A skin lesion imaged with a dermatoscope · by self-report, a personal history of skin cancer and a personal history of cancer · a moderate number of moles by the patient's own estimate · the patient says their skin reddens with sun exposure · imaged for a research study, with no referral diagnosis recorded · a male subject 77 years of age — 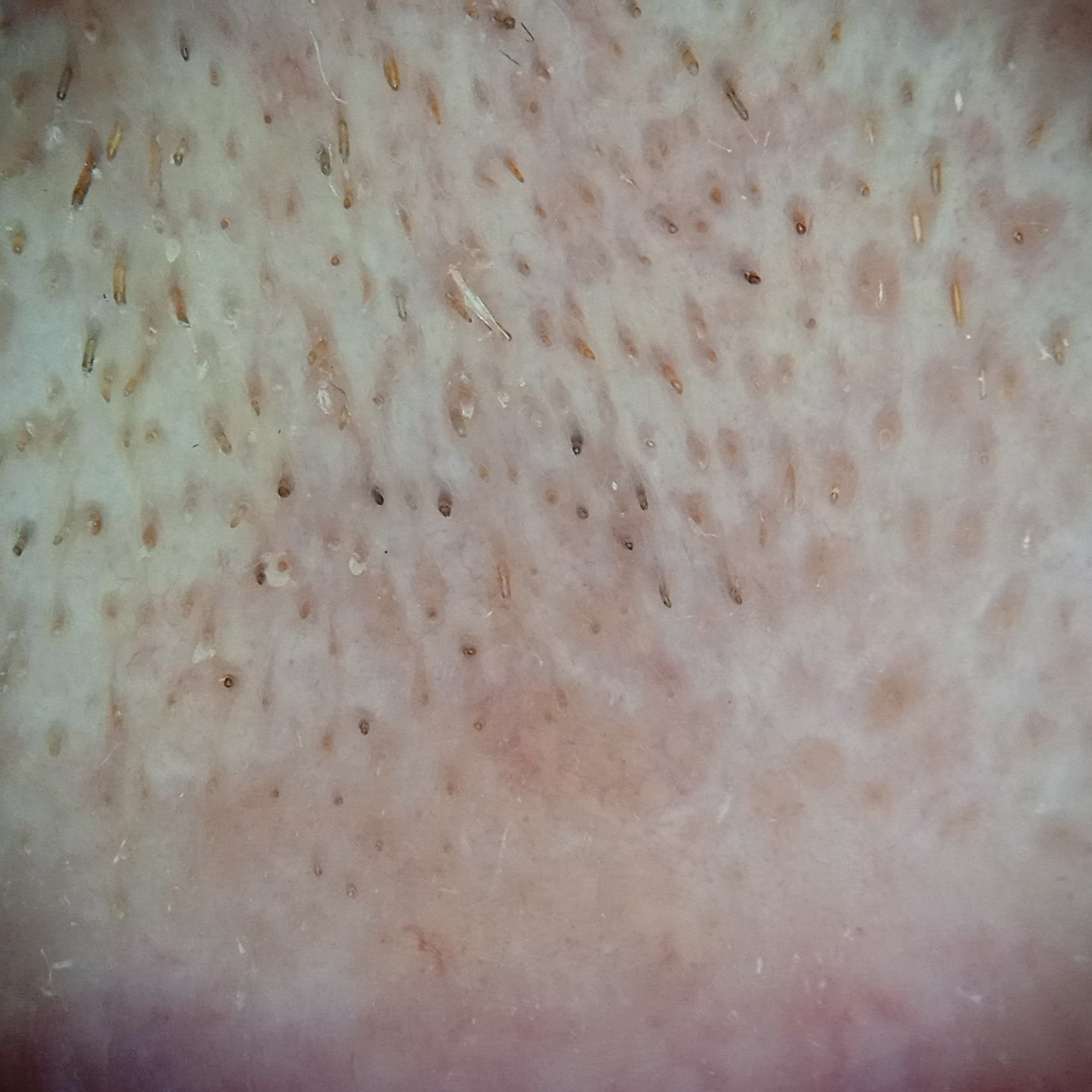The lesion involves the face. The lesion measures approximately 6.4 mm. The consensus diagnosis for this lesion was an actinic keratosis.